A skin lesion imaged with a dermatoscope:
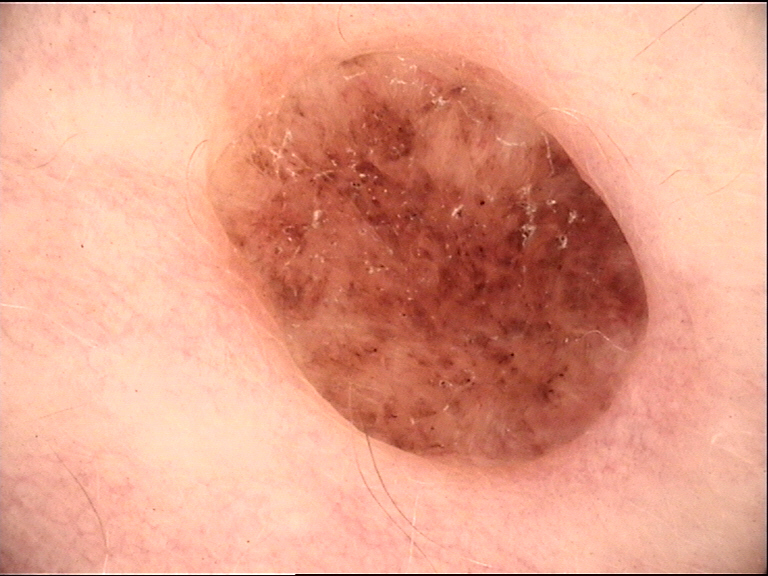Impression: Diagnosed as a dermal nevus.